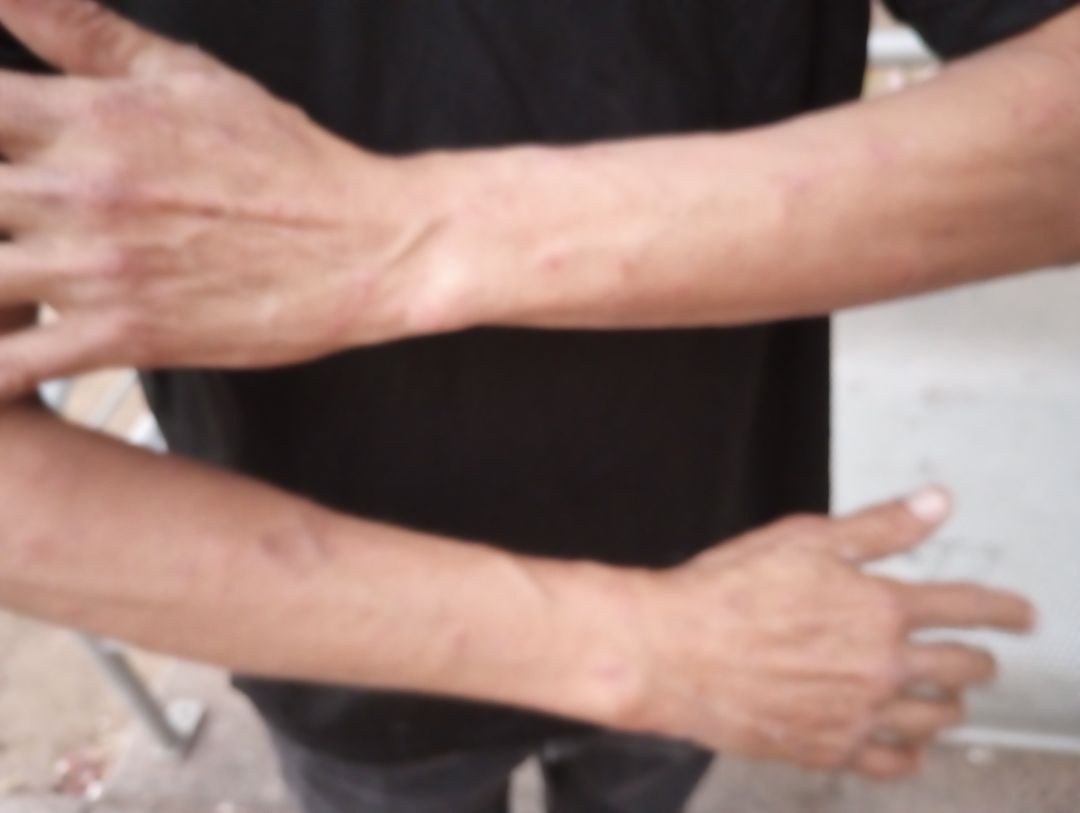assessment: unable to determine
photo taken: at a distance